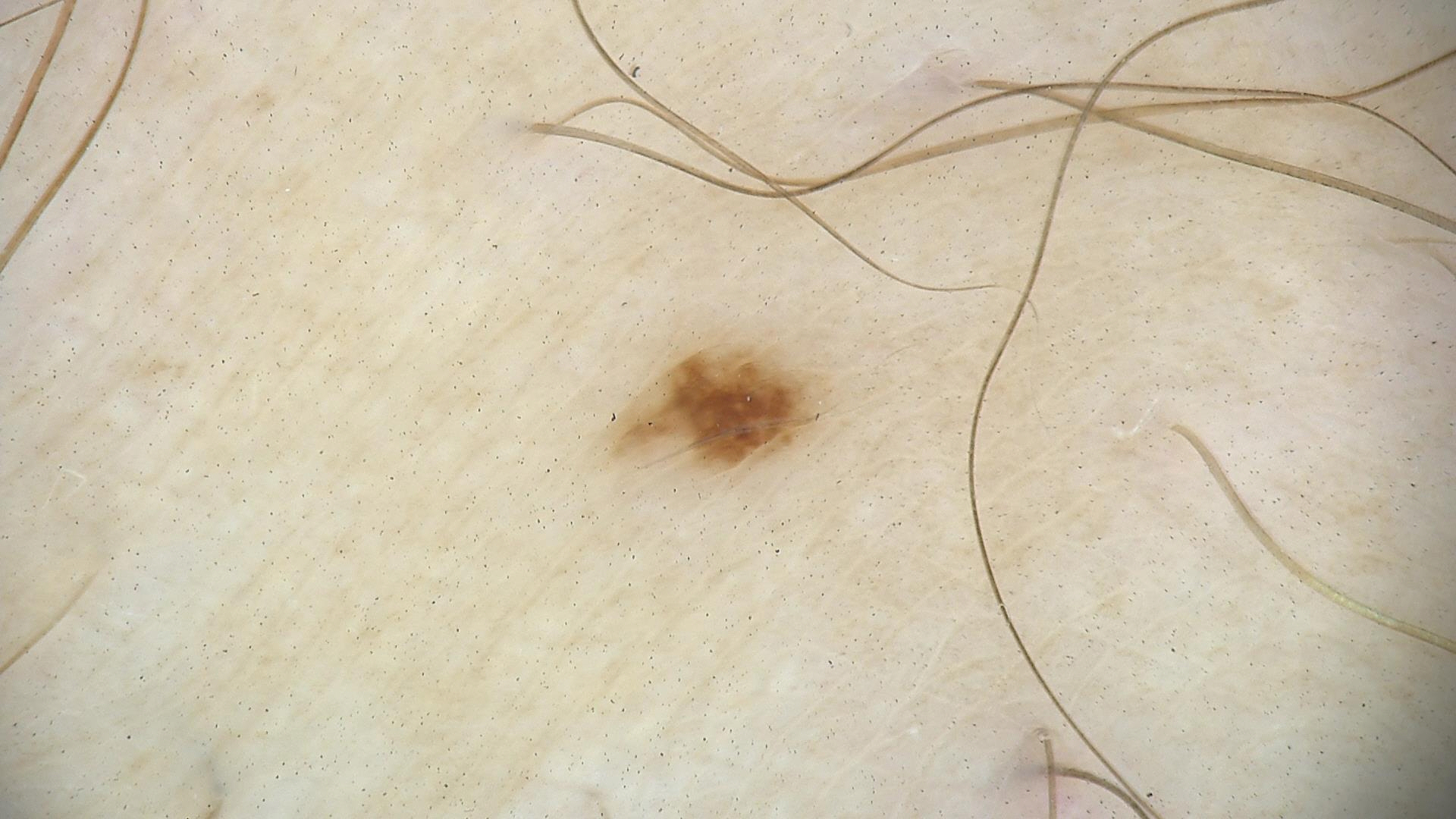Findings:
A skin lesion imaged with a dermatoscope.
Conclusion:
Diagnosed as a benign lesion — a dysplastic junctional nevus.